A dermoscopic close-up of a skin lesion:
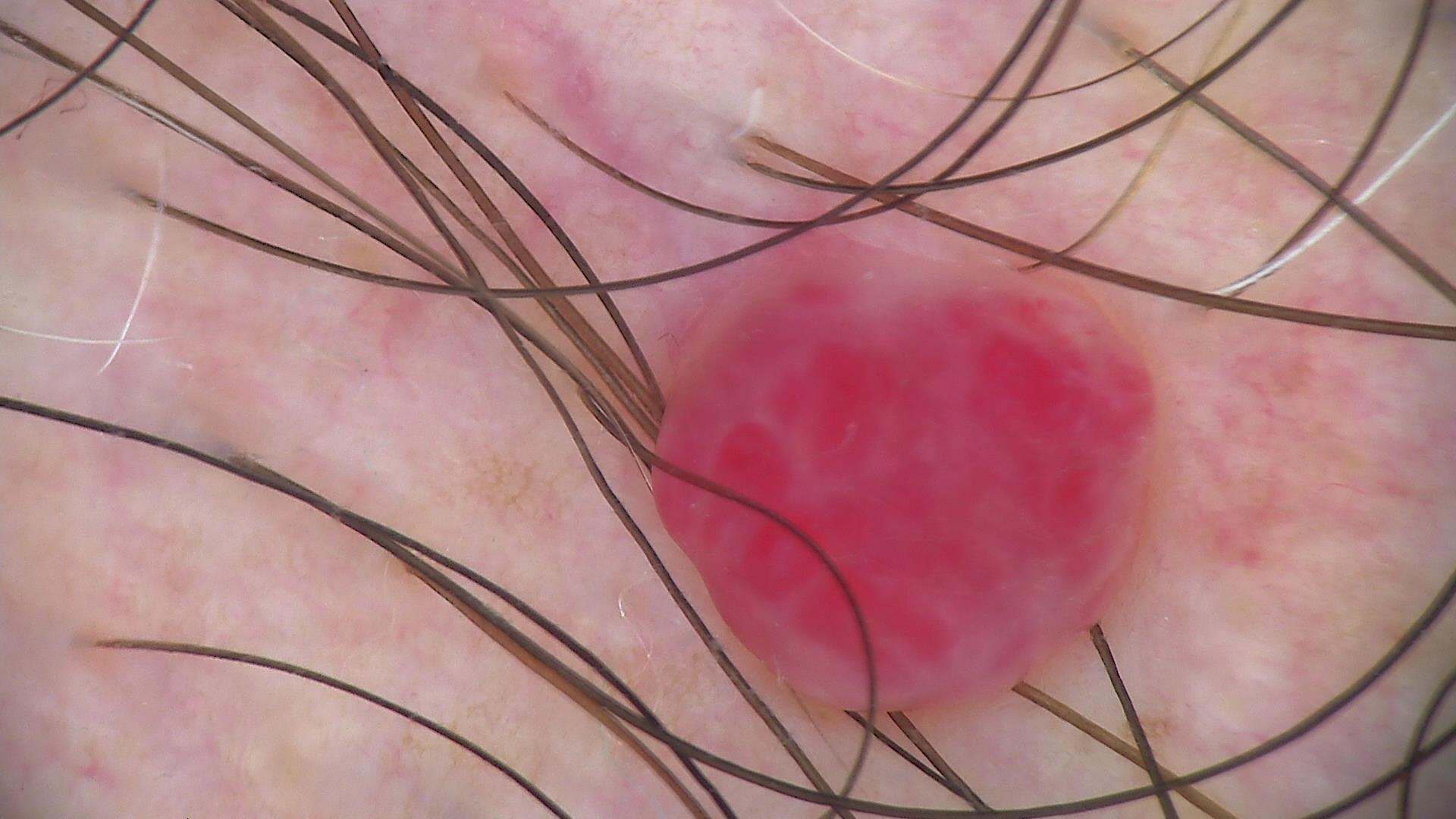The architecture is that of a vascular lesion. Labeled as a hemangioma.